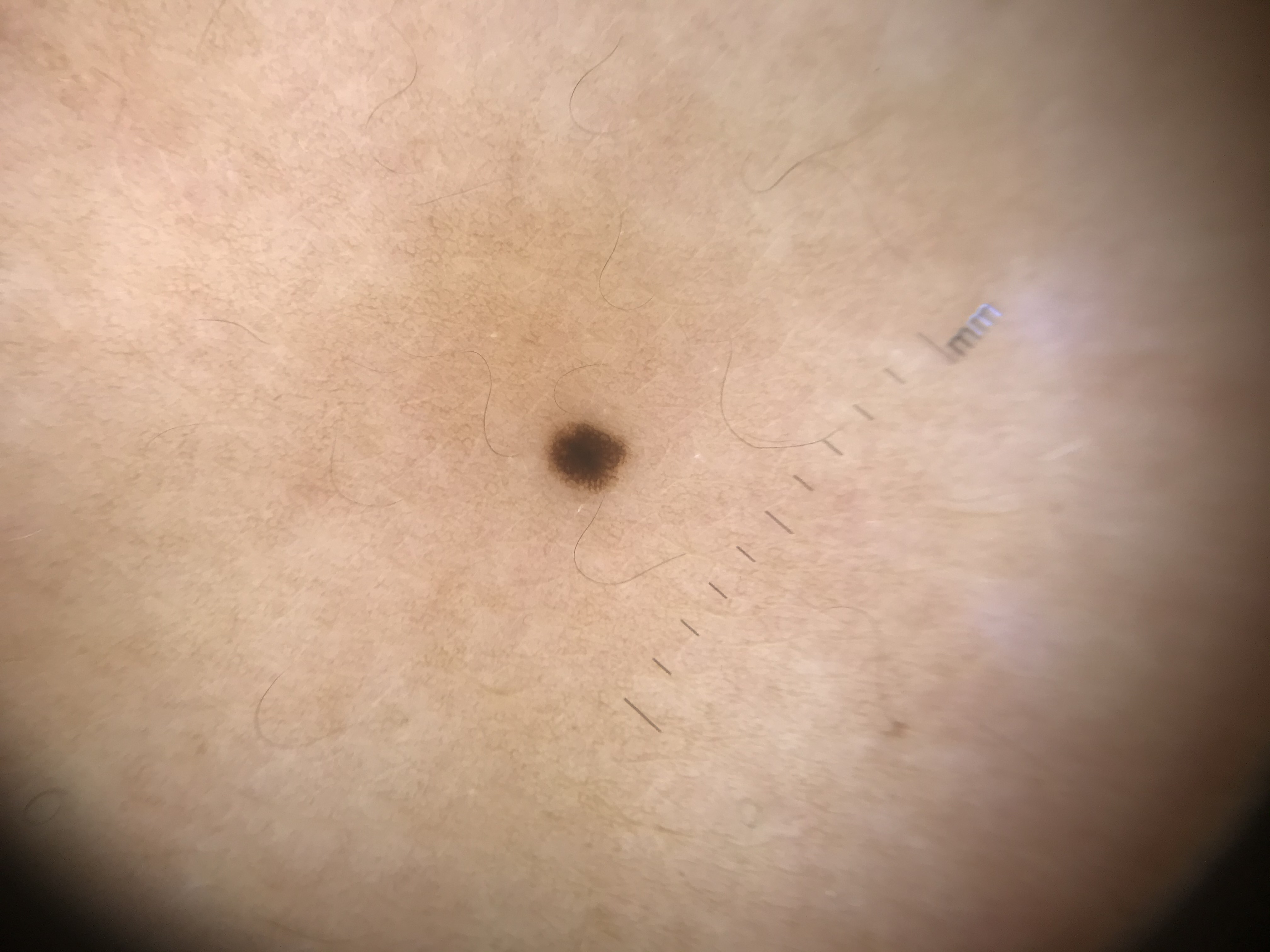label = junctional nevus (expert consensus)